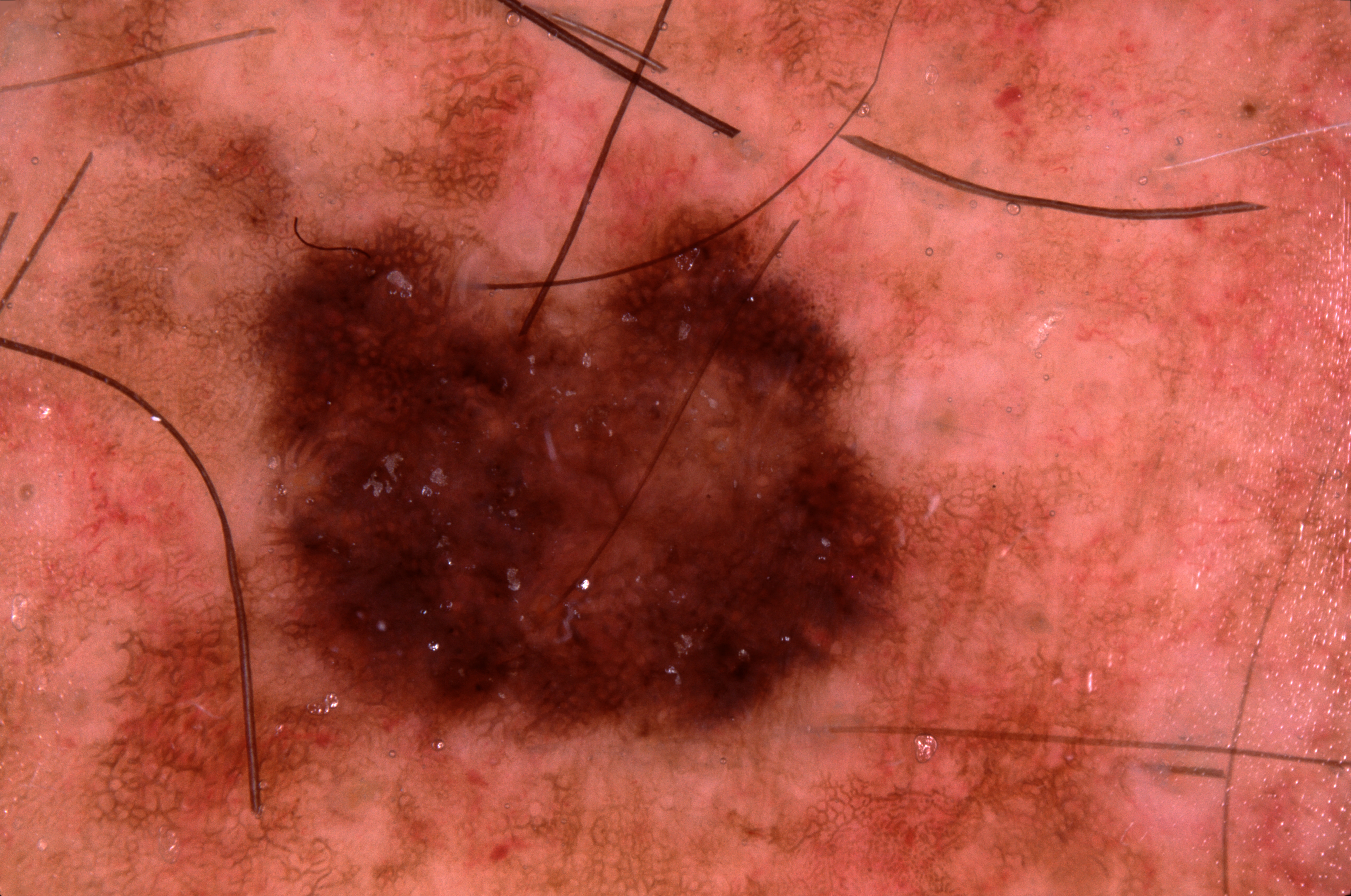A male subject, aged 63-67.
A dermoscopy image of a single skin lesion.
As (left, top, right, bottom), the lesion occupies the region <box>127, 196, 971, 784</box>.
The lesion occupies roughly 27% of the field.
On dermoscopy, the lesion shows pigment network, with no milia-like cysts, streaks, or negative network.
Histopathologically confirmed as a melanoma.